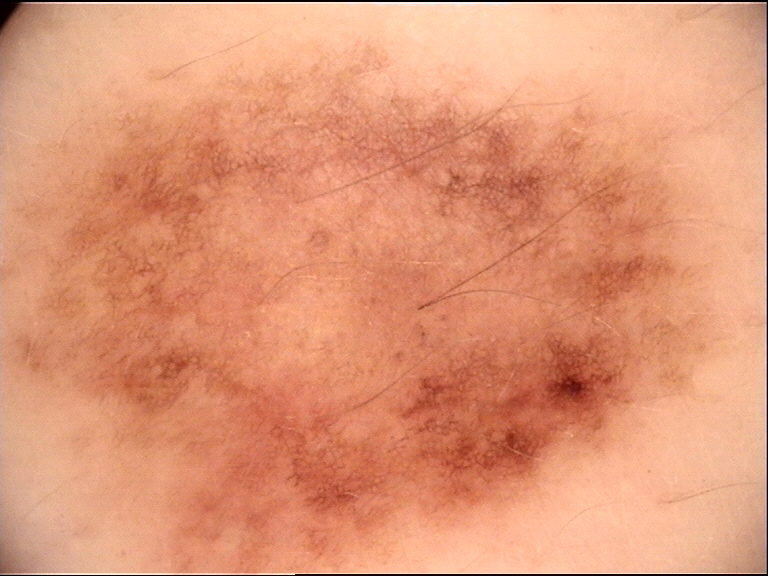imaging: dermatoscopy, assessment: dysplastic junctional nevus (expert consensus).